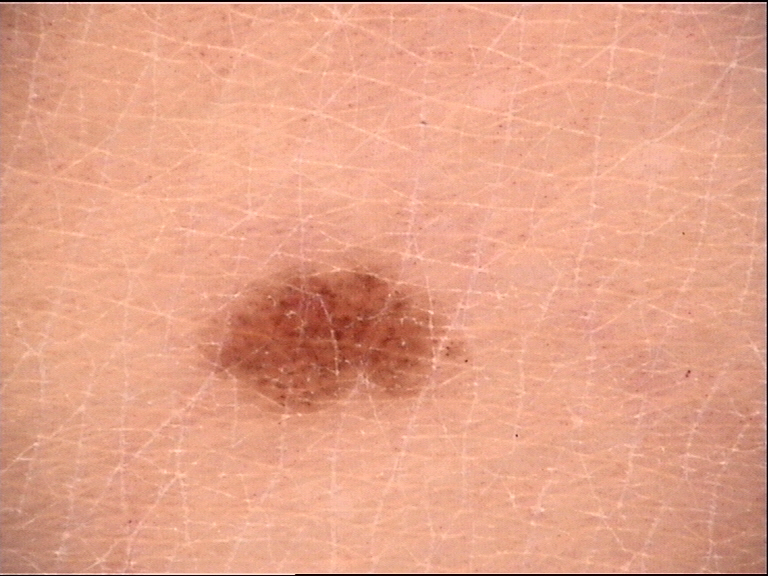Dermoscopy of a skin lesion.
Diagnosed as a banal lesion — a junctional nevus.